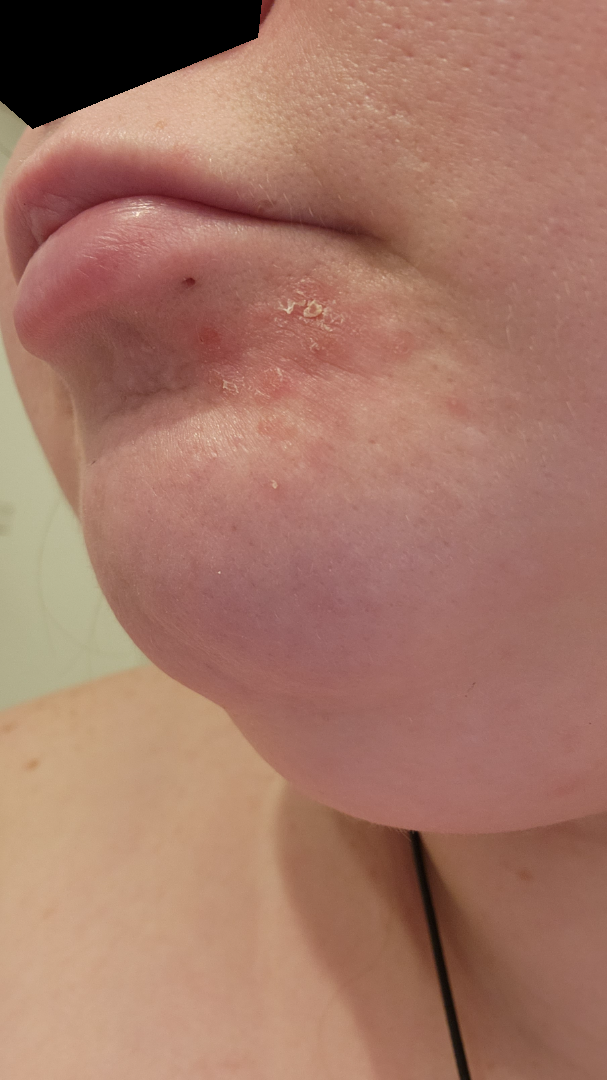assessment: the primary impression is Perioral Dermatitis.